The arm is involved; the photo was captured at an angle — 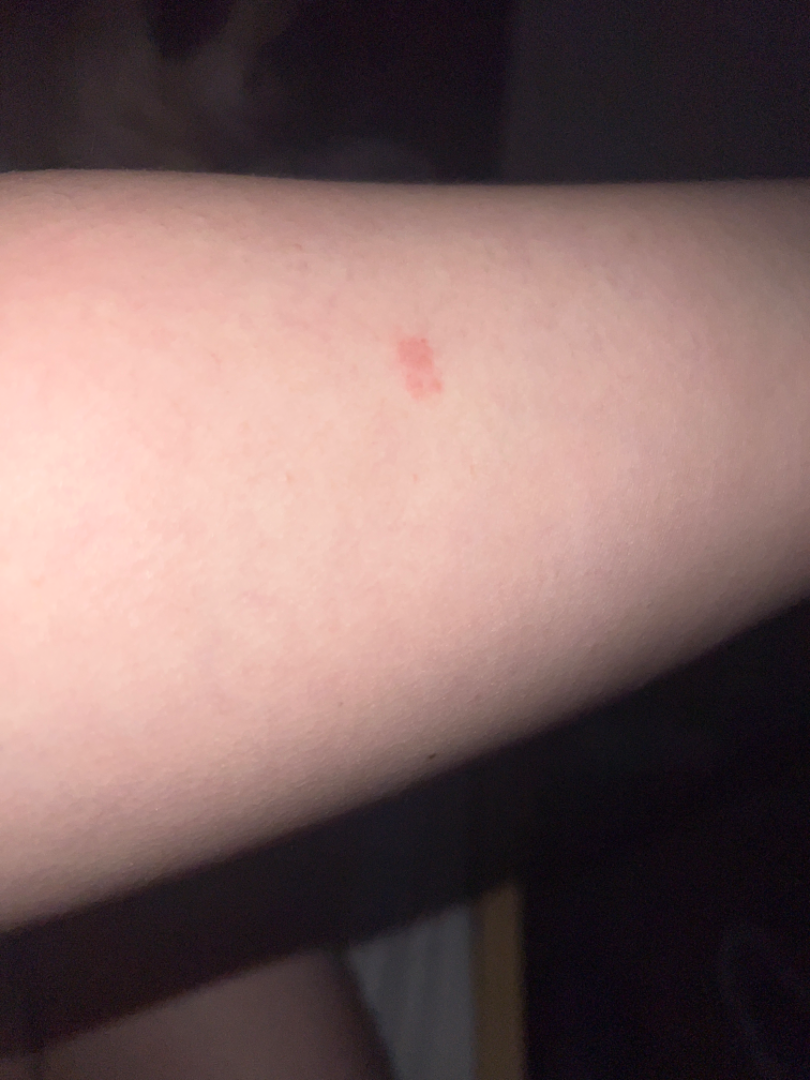{
  "texture": "raised or bumpy",
  "differential": {
    "leading": [
      "Eczema"
    ]
  }
}